A male subject, aged around 70. A skin lesion imaged with a dermatoscope:
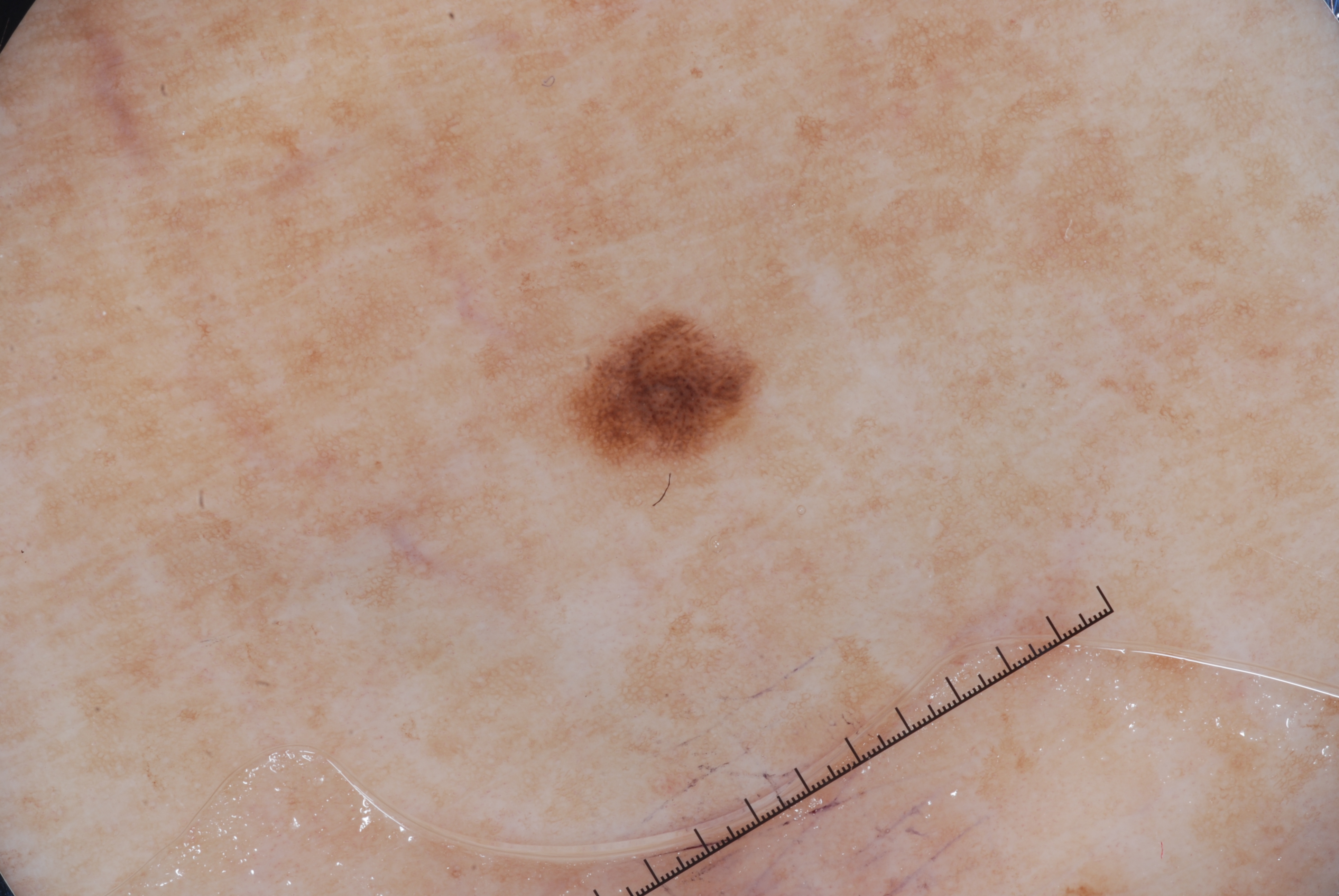Summary:
Dermoscopic examination shows pigment network. As (left, top, right, bottom), the lesion occupies the region <box>555, 305, 766, 478</box>.
Conclusion:
Diagnosed as a melanocytic nevus.